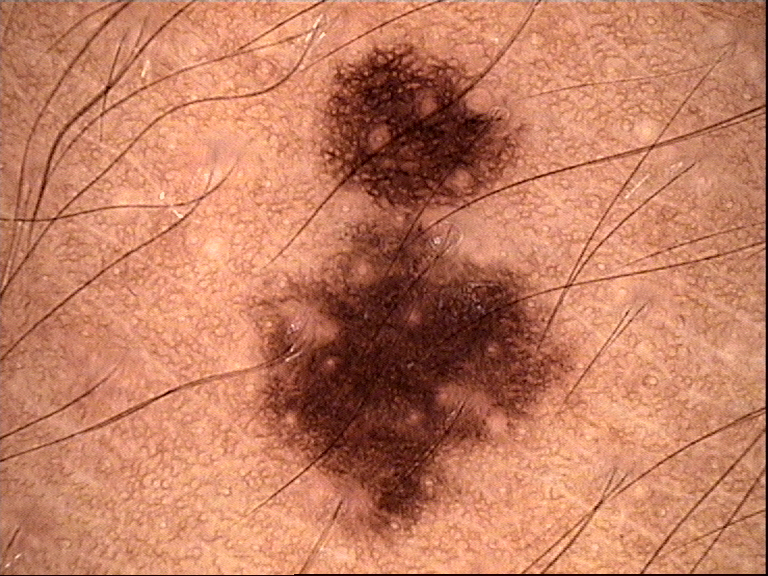The diagnostic label was a dysplastic junctional nevus.